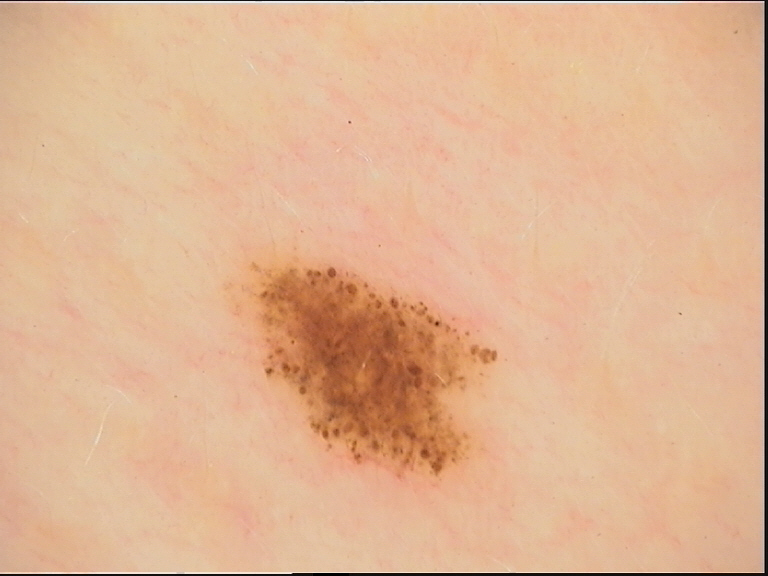image: dermoscopy
diagnosis: dysplastic junctional nevus (expert consensus)